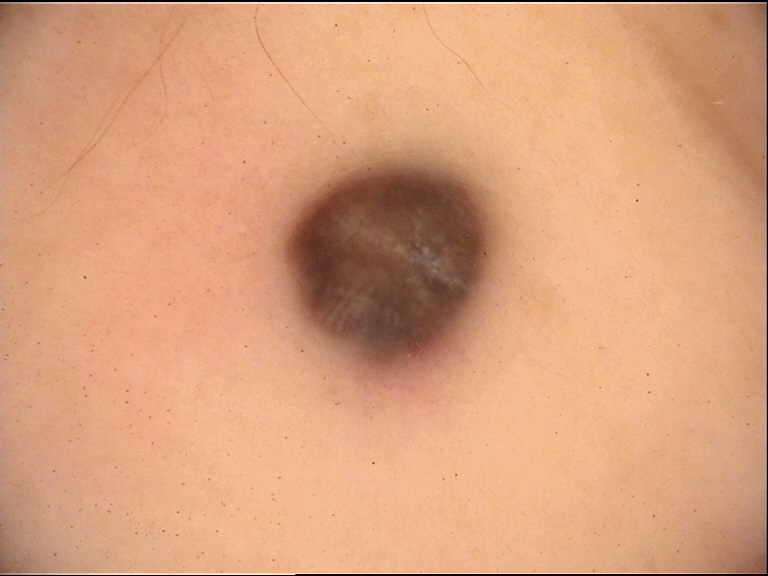{
  "diagnosis": {
    "name": "blue nevus",
    "code": "bdb",
    "malignancy": "benign",
    "super_class": "melanocytic",
    "confirmation": "expert consensus"
  }
}